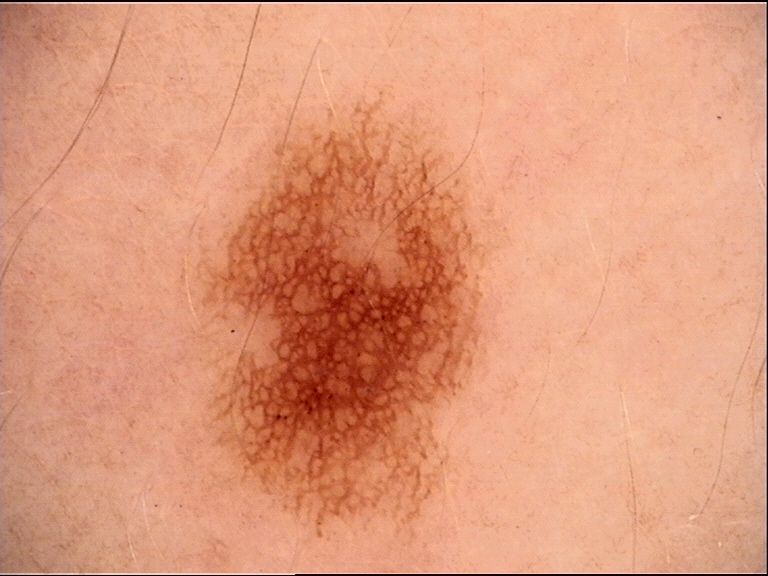Case:
* image: dermoscopy
* classification: banal
* diagnosis: junctional nevus (expert consensus)